A clinical photo of a skin lesion taken with a smartphone; a female subject 35 years of age.
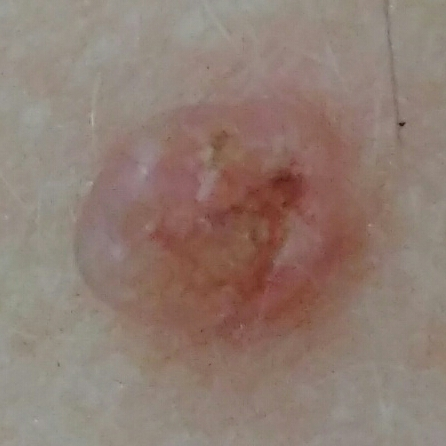The patient reports that the lesion has grown, itches, has bled, hurts, and is elevated. The biopsy diagnosis was a basal cell carcinoma.